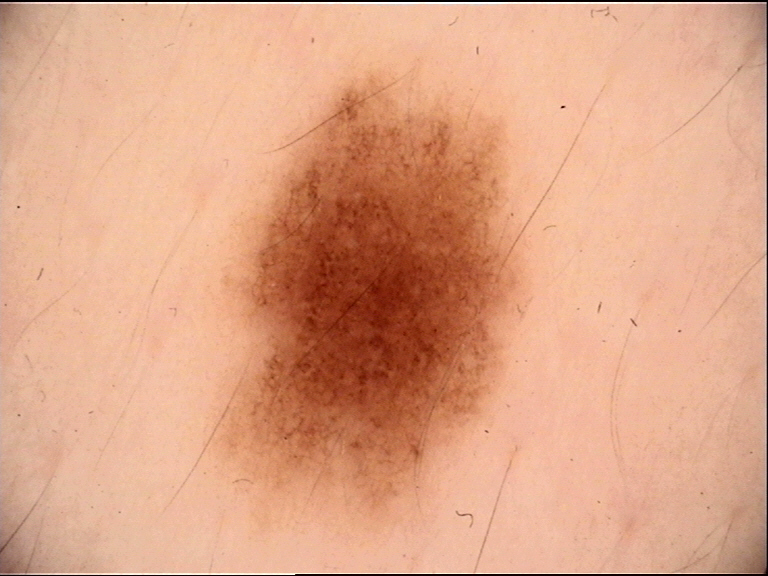image = dermatoscopy; diagnostic label = dysplastic junctional nevus (expert consensus).